Symptoms reported: itching. The contributor notes the lesion is raised or bumpy. Male contributor, age 30–39. This is a close-up image. The patient described the issue as a rash. The leg is involved:
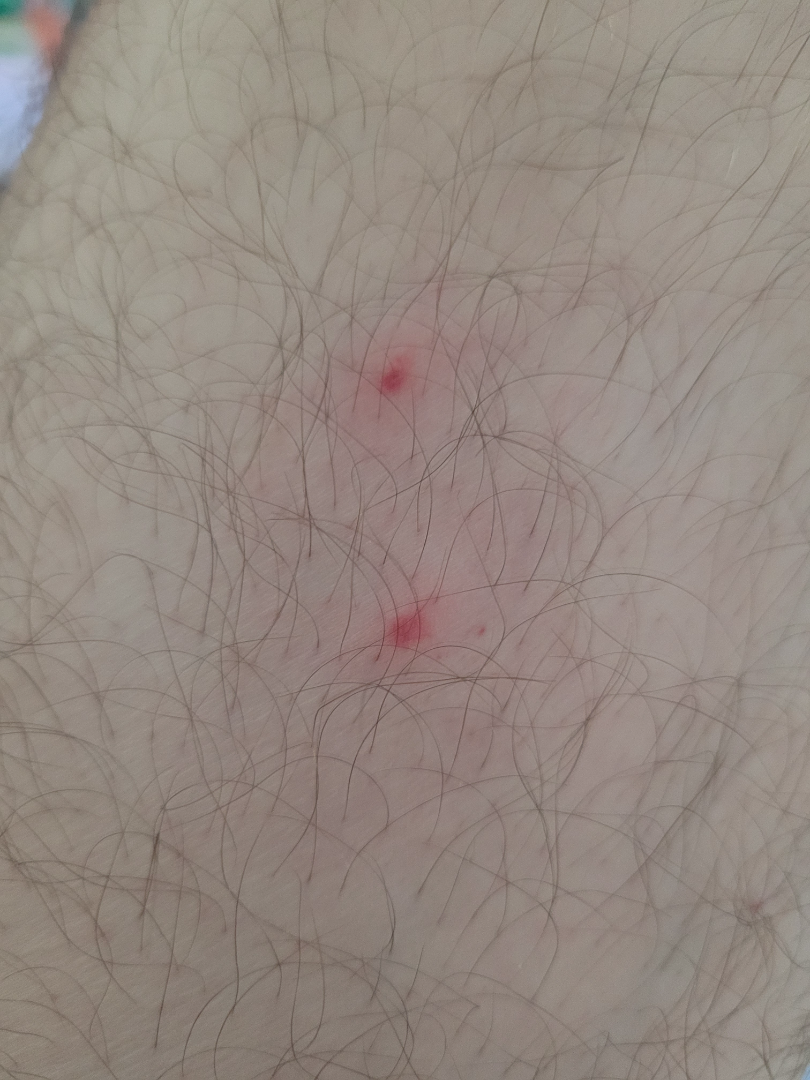Impression: The skin findings could not be characterized from the image.